A dermoscopic photograph of a skin lesion:
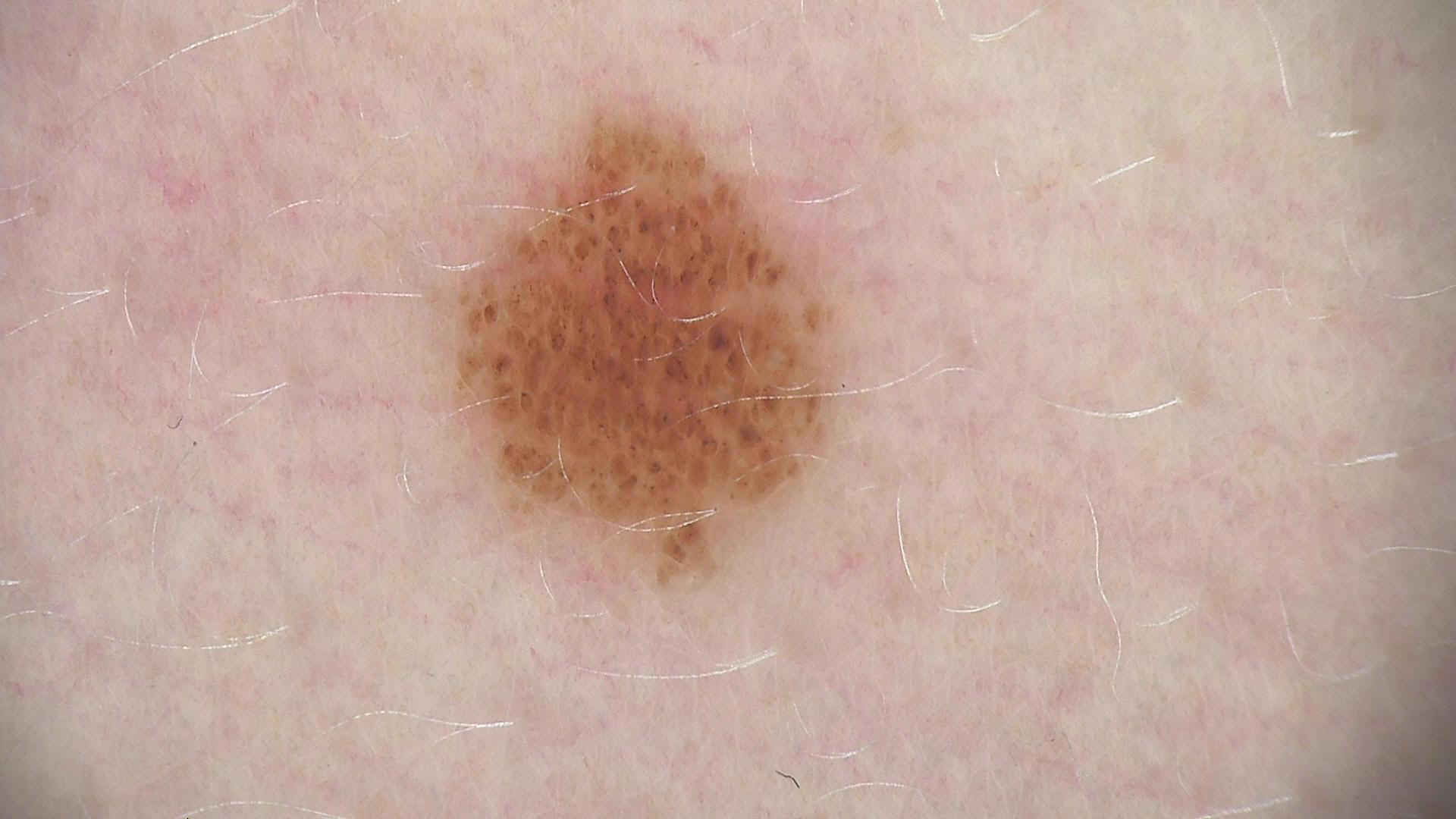diagnosis:
  name: dysplastic junctional nevus
  code: jd
  malignancy: benign
  super_class: melanocytic
  confirmation: expert consensus